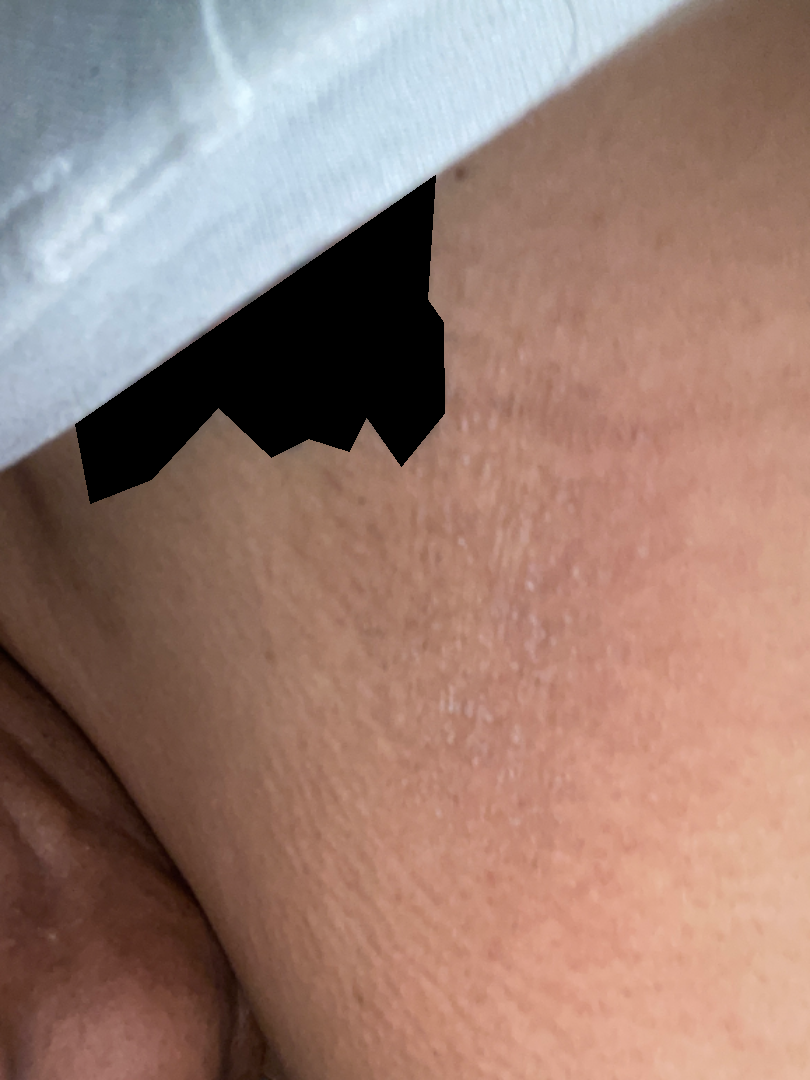Q: What is the differential diagnosis?
A: Eczema (100%)